The front of the torso, arm, back of the hand and leg are involved. The photograph was taken at an angle — 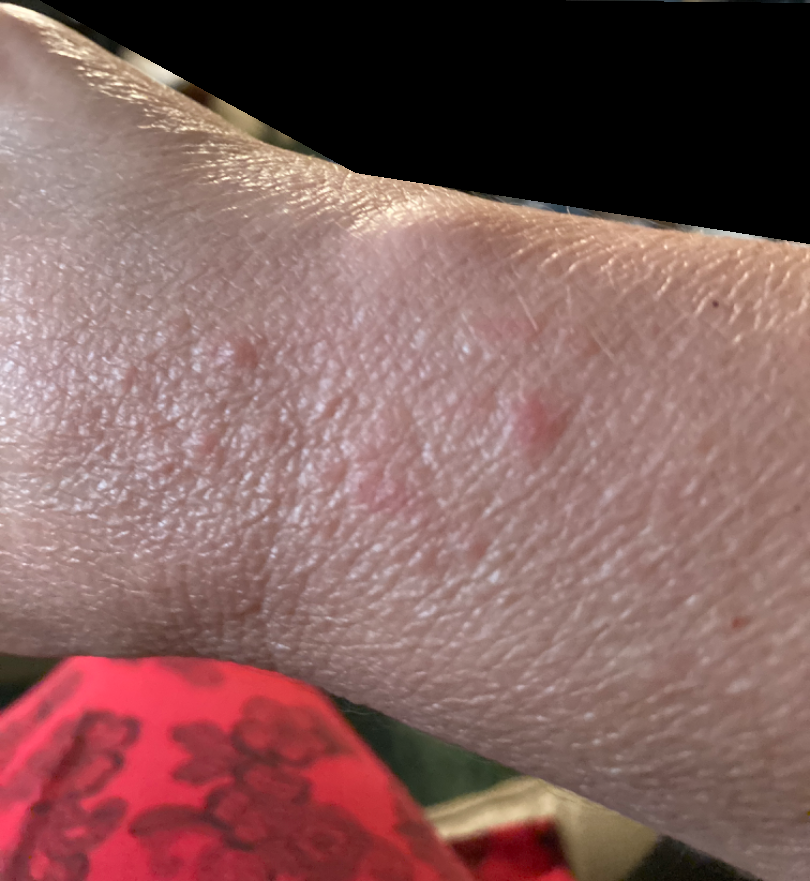{"differential": {"leading": ["Eczema"], "considered": ["Tinea", "Psoriasis"]}}